The patient described the issue as a rash · an image taken at an angle · no constitutional symptoms were reported · present for three to twelve months · texture is reported as rough or flaky, raised or bumpy and fluid-filled · symptoms reported: burning, itching and bothersome appearance · female contributor, age 18–29.
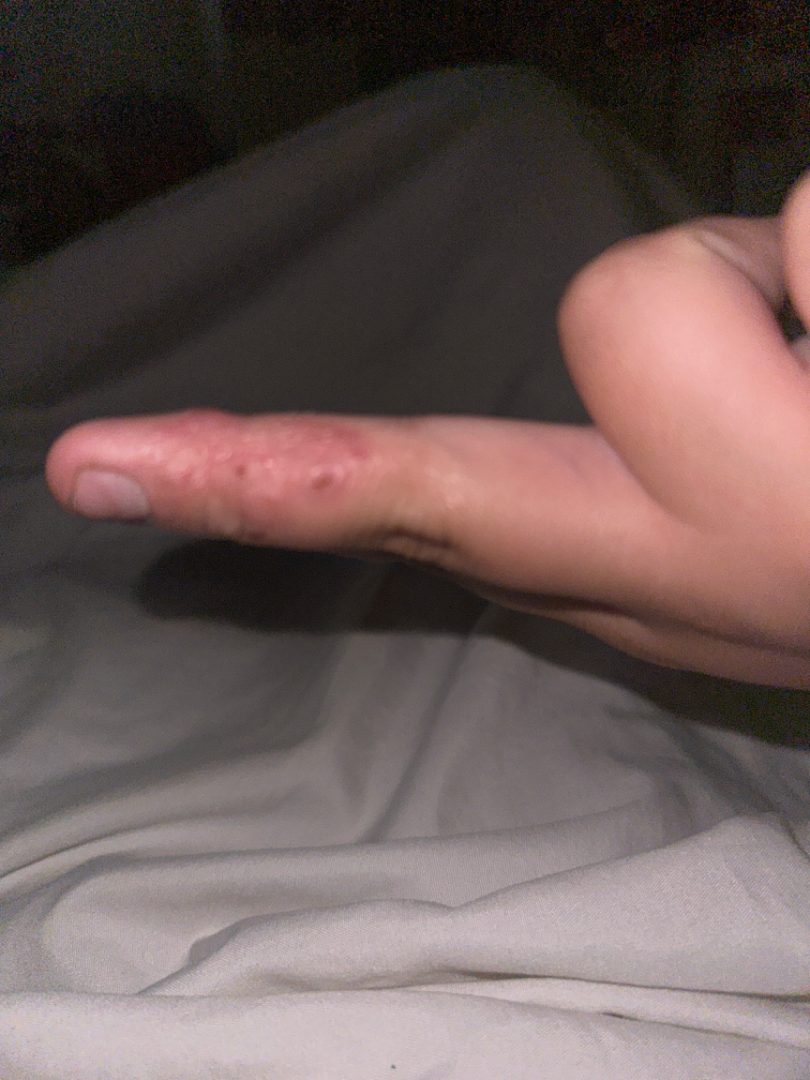The image was not sufficient for the reviewer to characterize the skin condition.